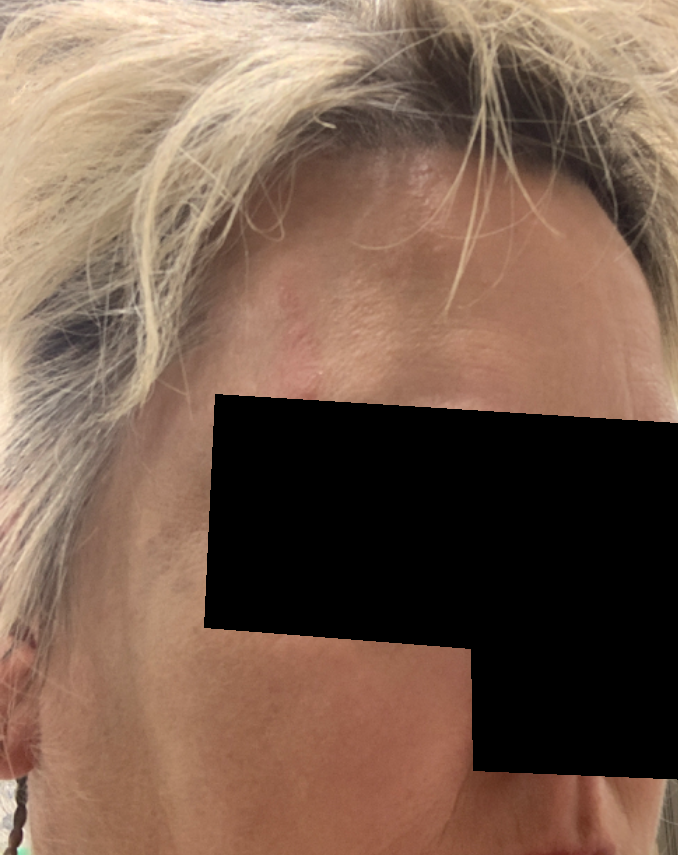Q: What was the assessment?
A: unable to determine